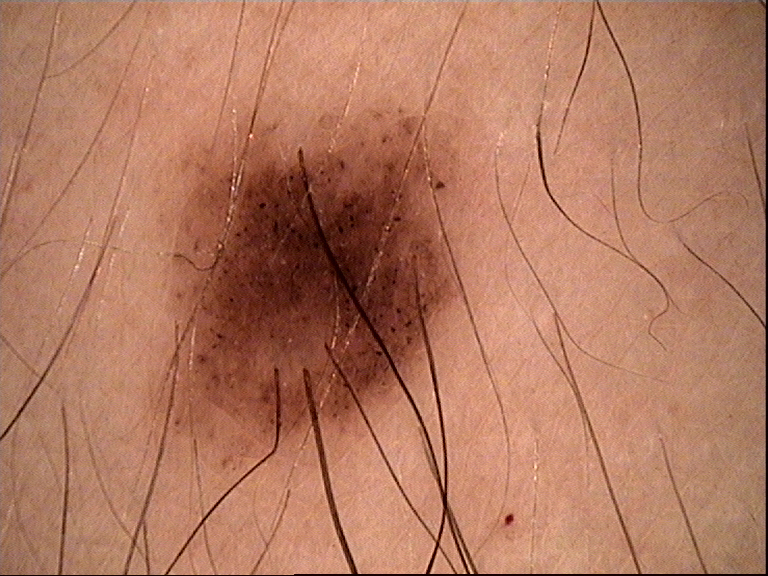Classified as a banal lesion — a compound nevus.